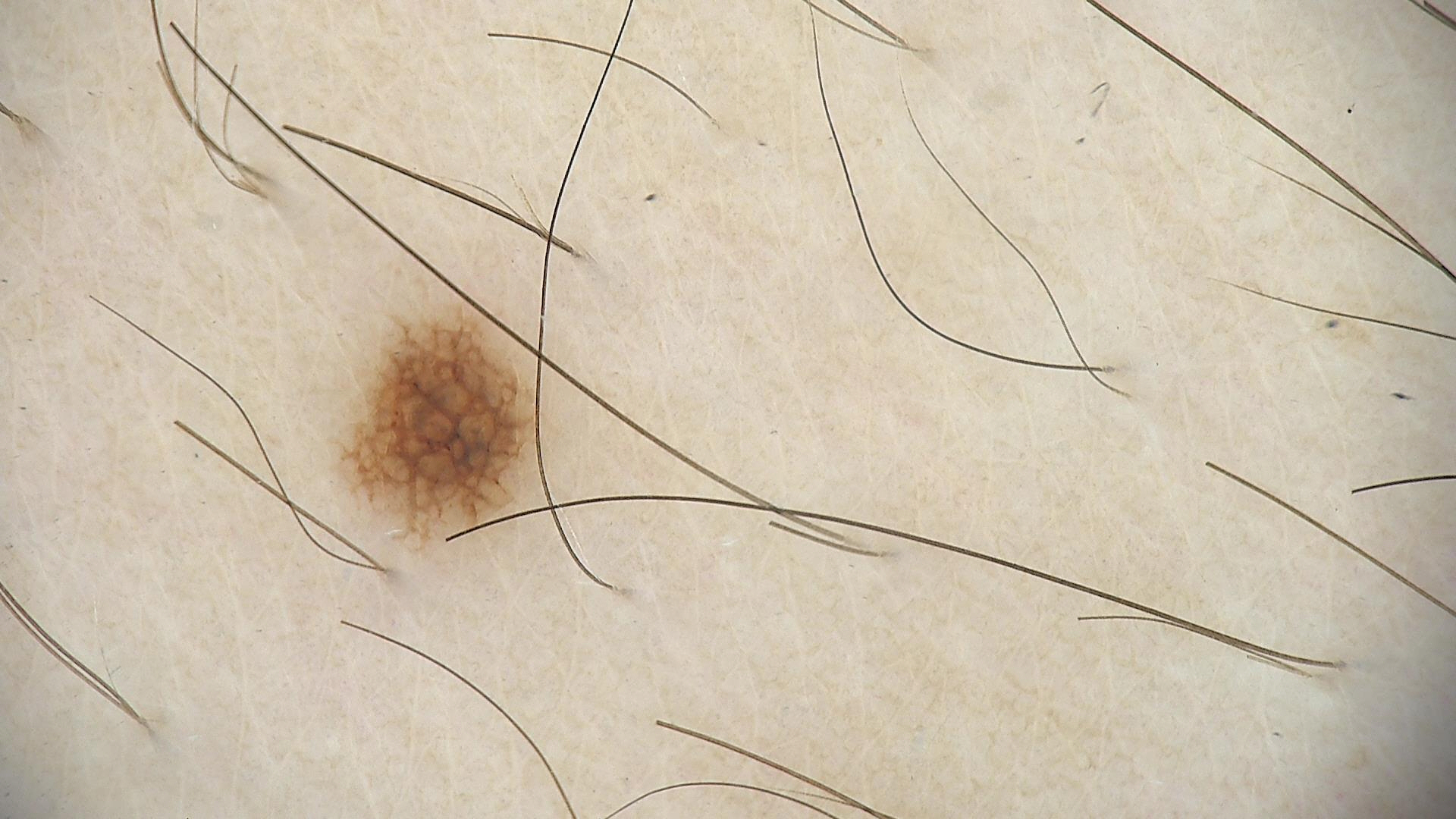A skin lesion imaged with a dermatoscope. Diagnosed as a dysplastic junctional nevus.